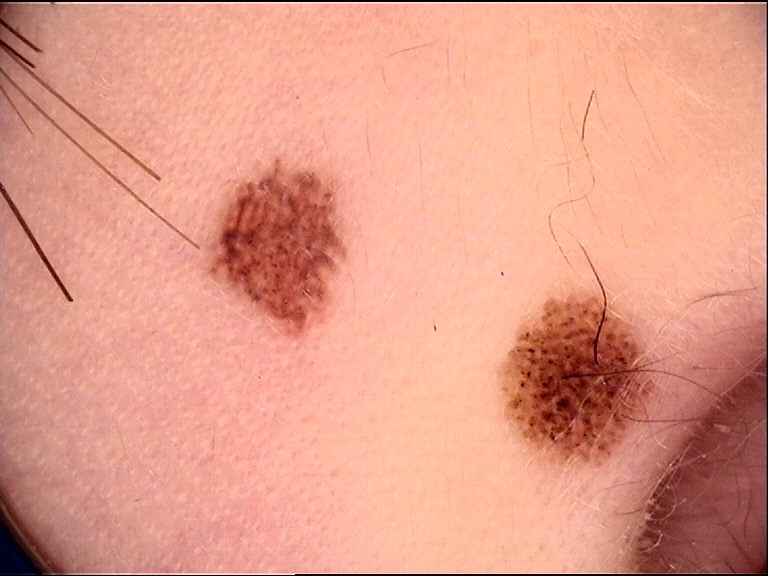Dermoscopy of a skin lesion. This is a banal, compound lesion. Diagnosed as a Miescher nevus.